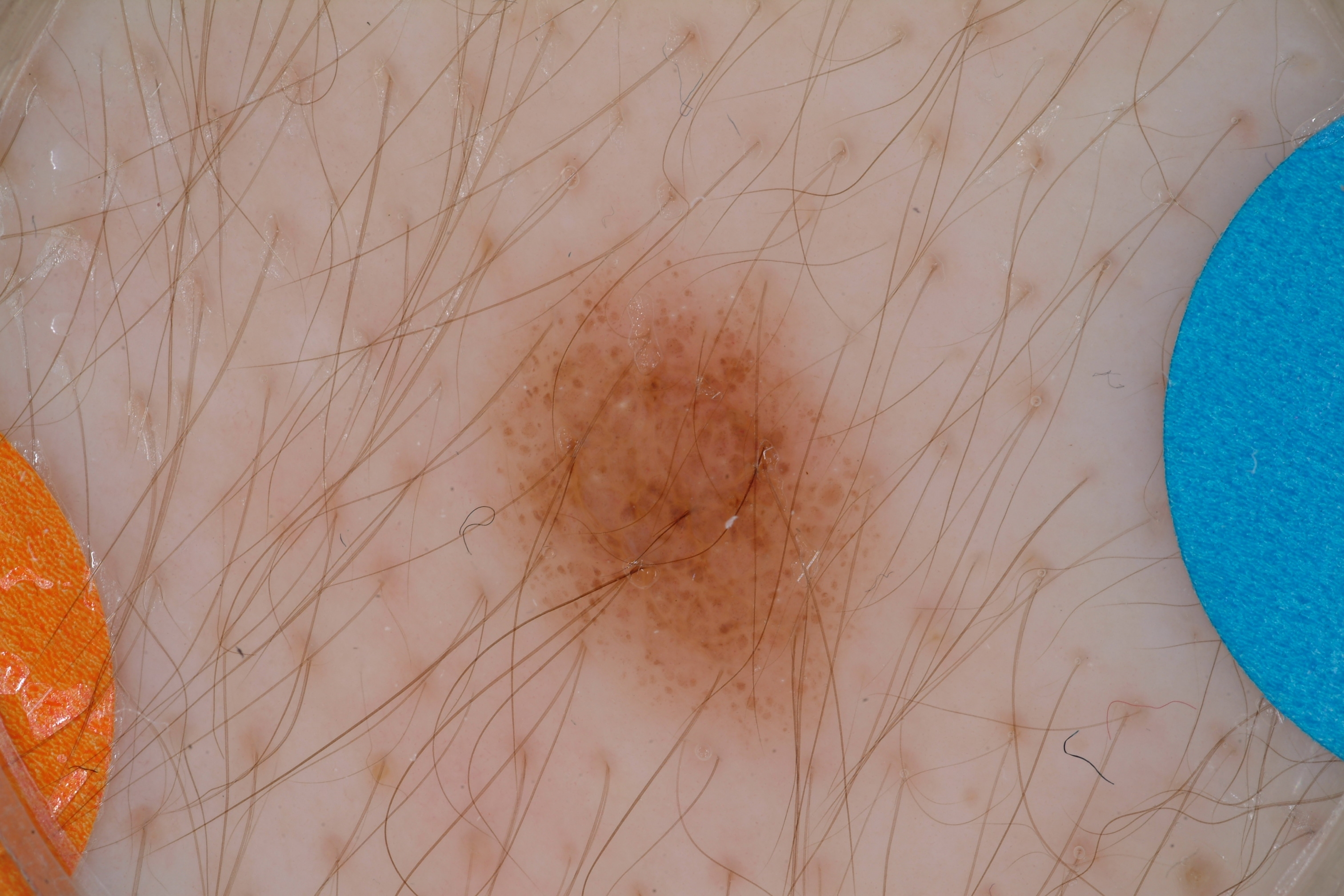Image and clinical context:
A male subject, about 15 years old. A dermoscopic image of a skin lesion. The lesion covers approximately 13% of the dermoscopic field. The lesion's extent is box(472, 237, 895, 765). Dermoscopically, the lesion shows globules, milia-like cysts, and negative network, with no pigment network or streaks.
Impression:
The lesion was assessed as a melanocytic nevus.